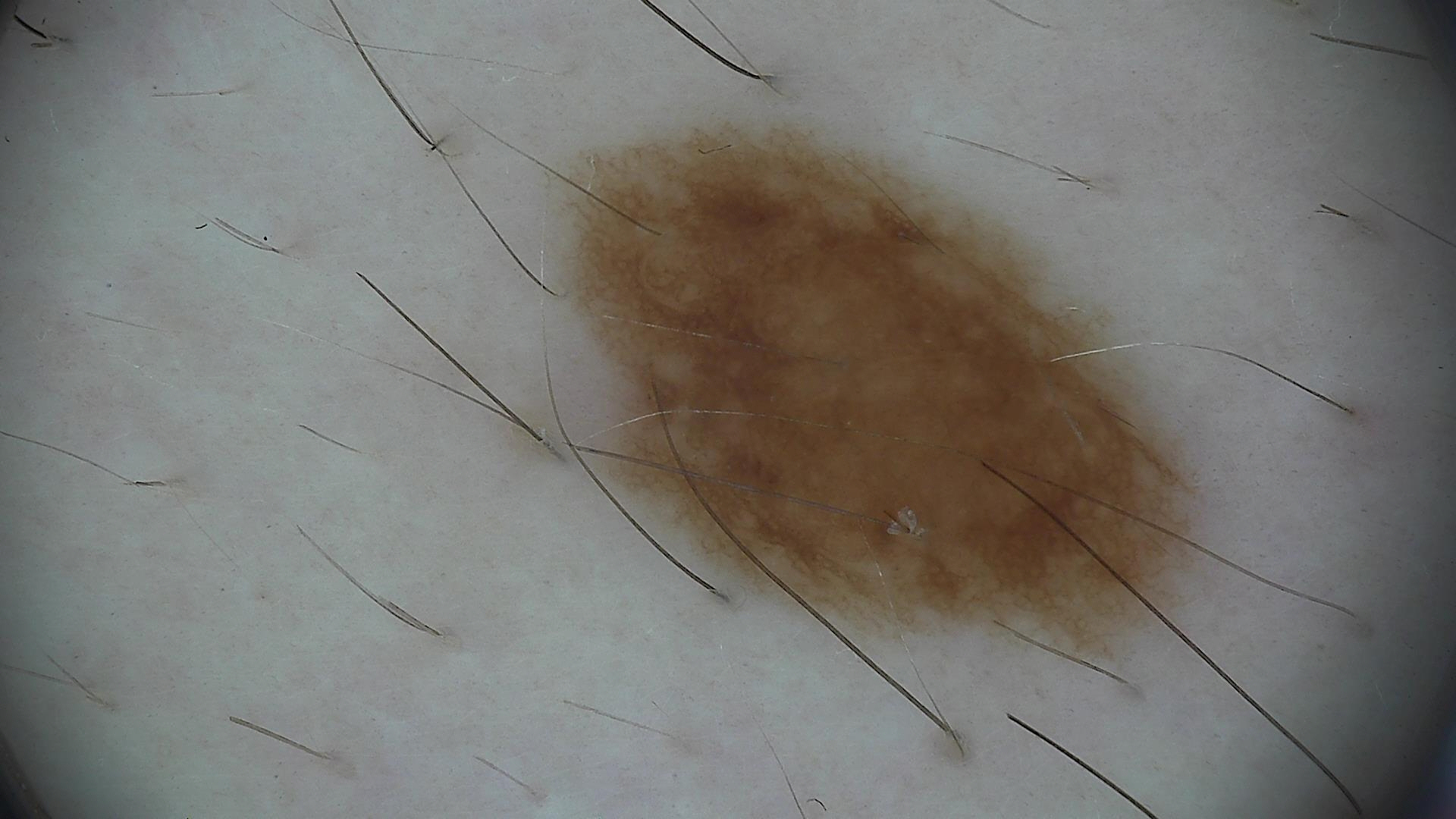diagnostic label: dysplastic junctional nevus (expert consensus).